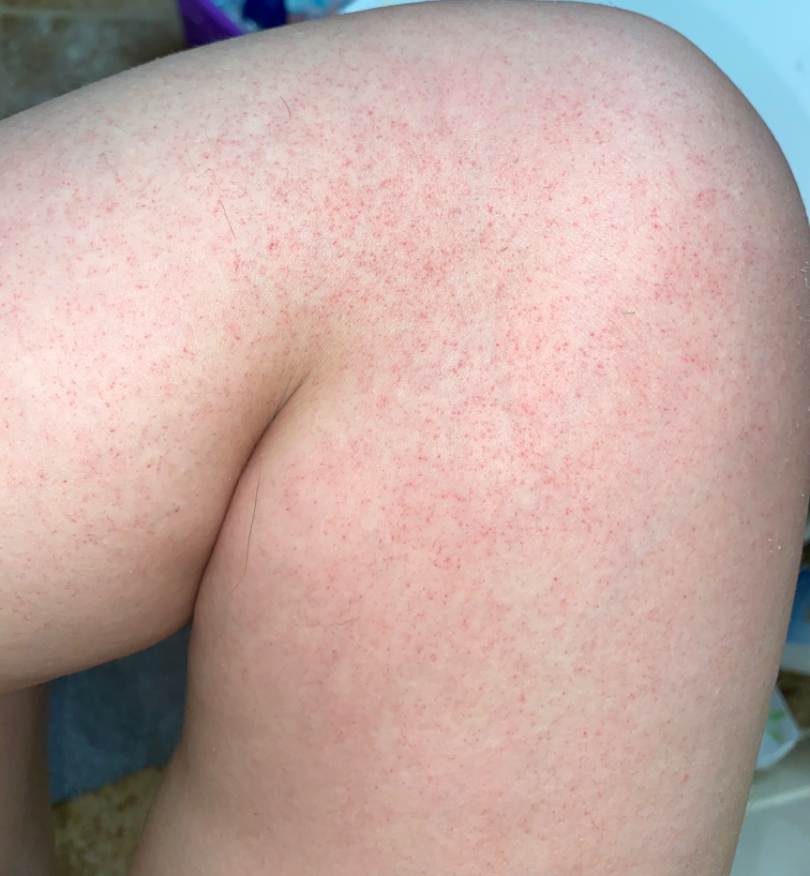<dermatology_case>
  <patient>female, age 18–29</patient>
  <body_site>leg</body_site>
  <shot_type>close-up</shot_type>
  <differential>
    <Purpura>1.0</Purpura>
  </differential>
</dermatology_case>